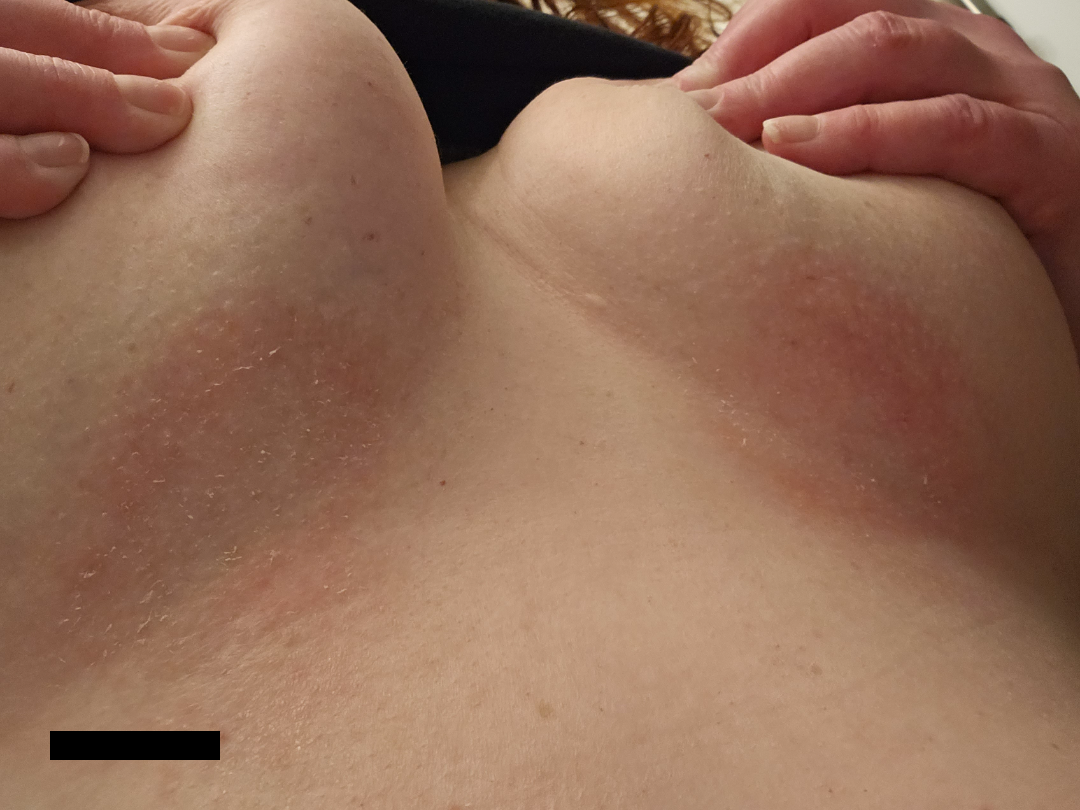No constitutional symptoms were reported. Symptoms reported: pain. The contributor notes the lesion is rough or flaky. The subject is 50–59, female. A close-up photograph. The contributor notes the condition has been present for less than one week. Located on the front of the torso. The leading impression is Intertrigo; also consider Psoriasis; lower on the differential is Candida; less likely is Seborrheic Dermatitis.